The head or neck, arm, leg, back of the hand, front of the torso and top or side of the foot are involved; the photograph was taken at a distance; the lesion is associated with enlargement, itching and burning; FST III; reported duration is about one day; the patient considered this a rash; the contributor is 18–29, female:
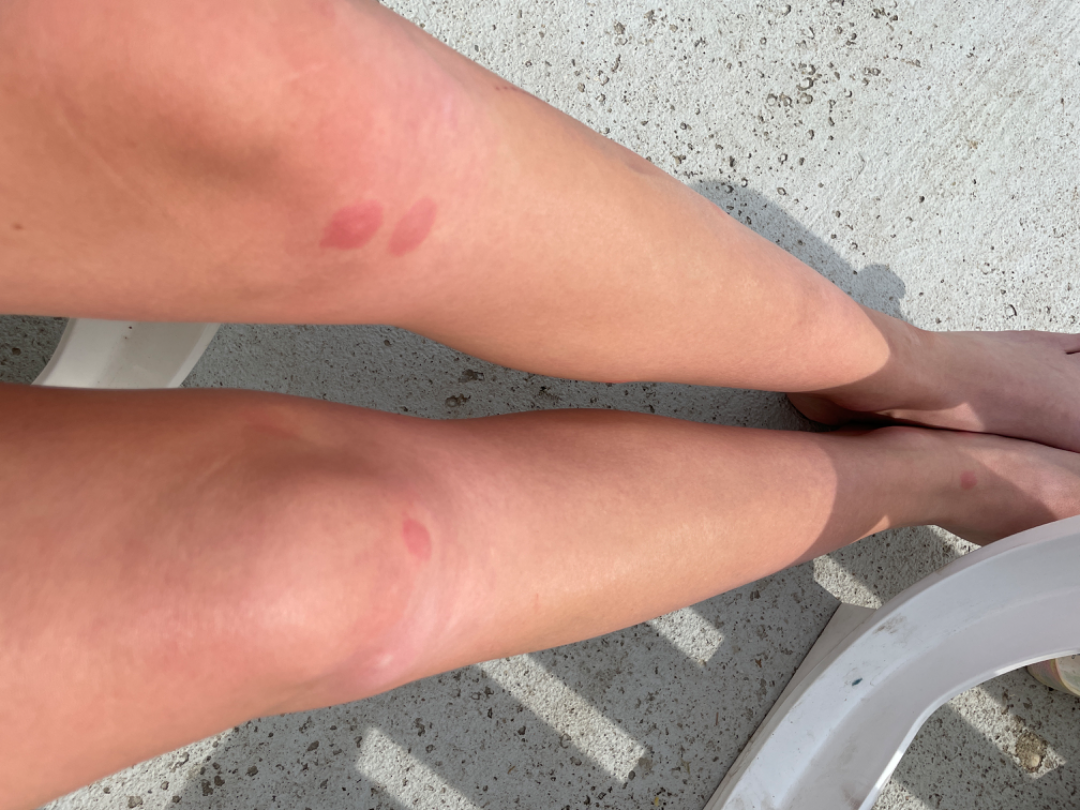Review:
The case was indeterminate on photographic review.